Close-up view; the patient is 50–59, male: 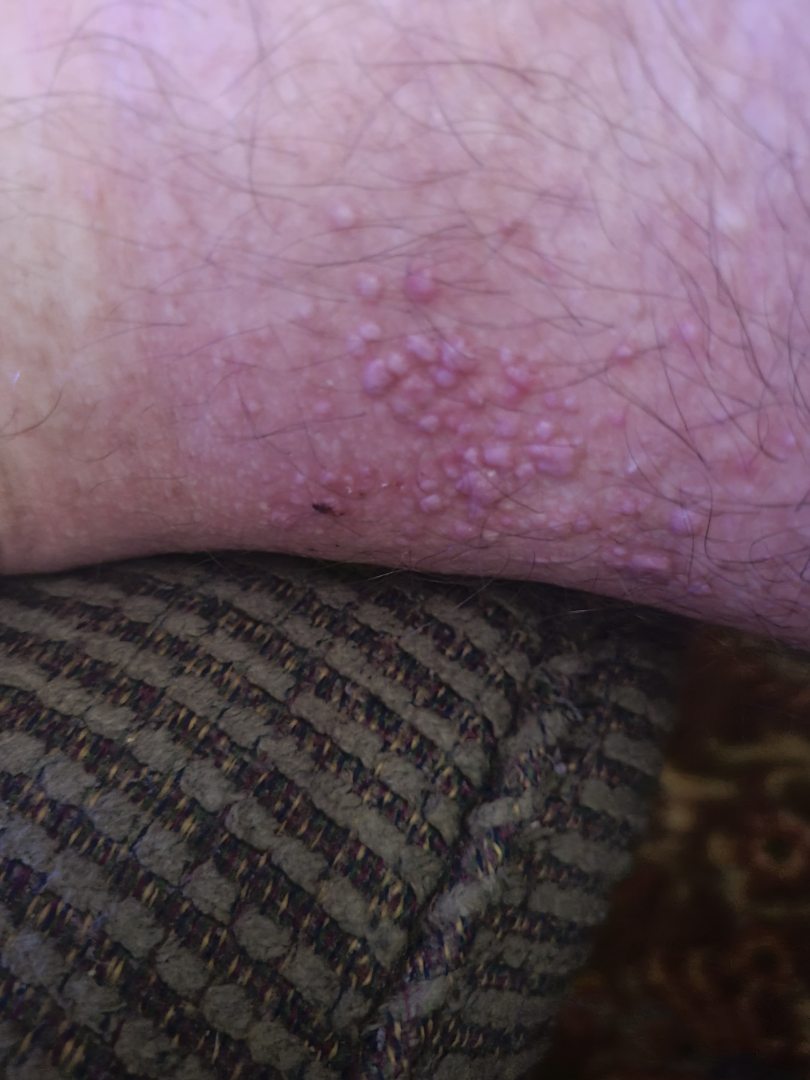Patient information: Symptoms reported: bothersome appearance and enlargement. Review: Favoring Molluscum Contagiosum; also on the differential is Verruca vulgaris; less probable is Calcinosis cutis.